The patient reports enlargement, burning and bothersome appearance; the patient described the issue as a rash; an image taken at a distance; the patient also reports mouth sores; the affected area is the head or neck; texture is reported as raised or bumpy and rough or flaky; the patient reports the condition has been present for one to three months; the contributor is male — 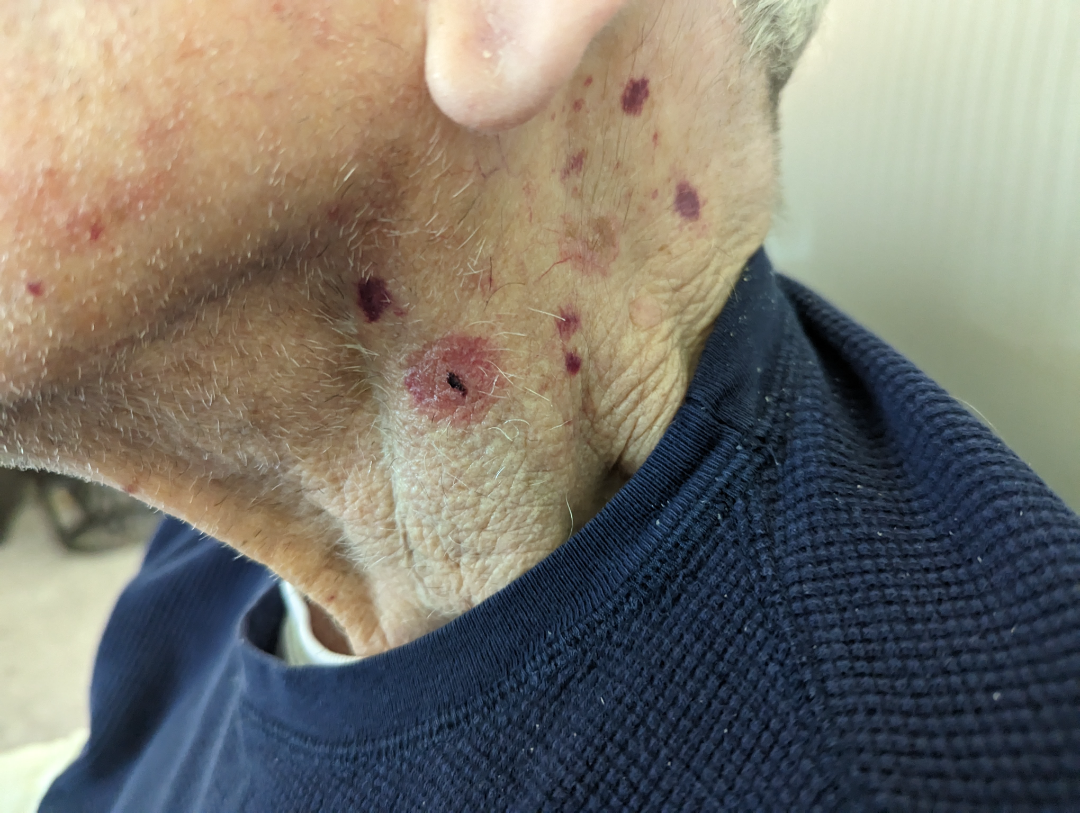Findings:
Three independent reviewers: favoring Purpura; also raised was ecchymoses.